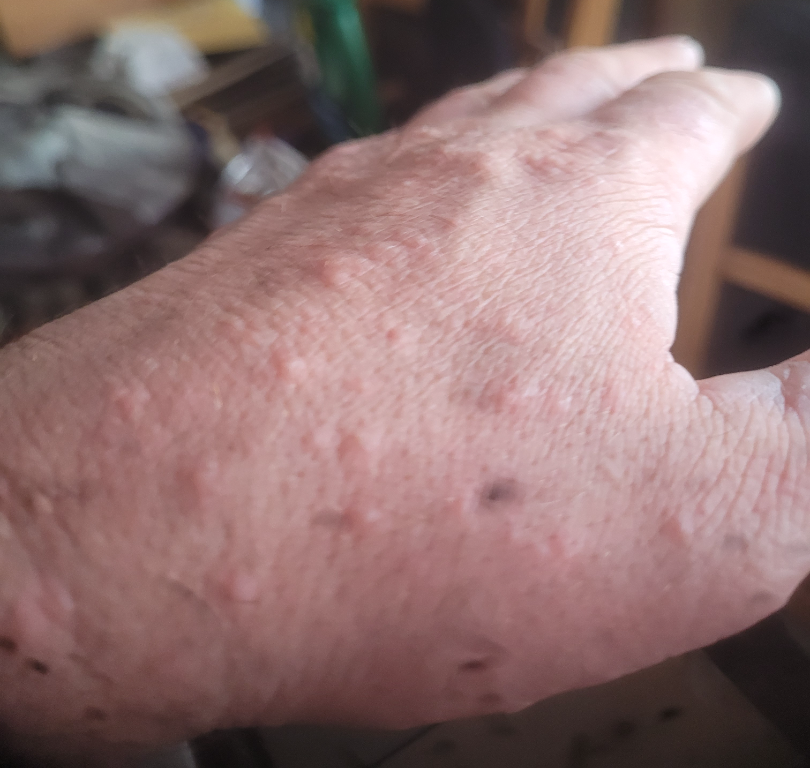The patient is male.
The affected area is the arm, front of the torso, leg, palm, head or neck, back of the torso and back of the hand.
The photo was captured at an angle.
Contact dermatitis (1.00).